Present for about one day · the contributor is a male aged 40–49 · reported lesion symptoms include bothersome appearance · the patient described the issue as a rash · this is a close-up image: 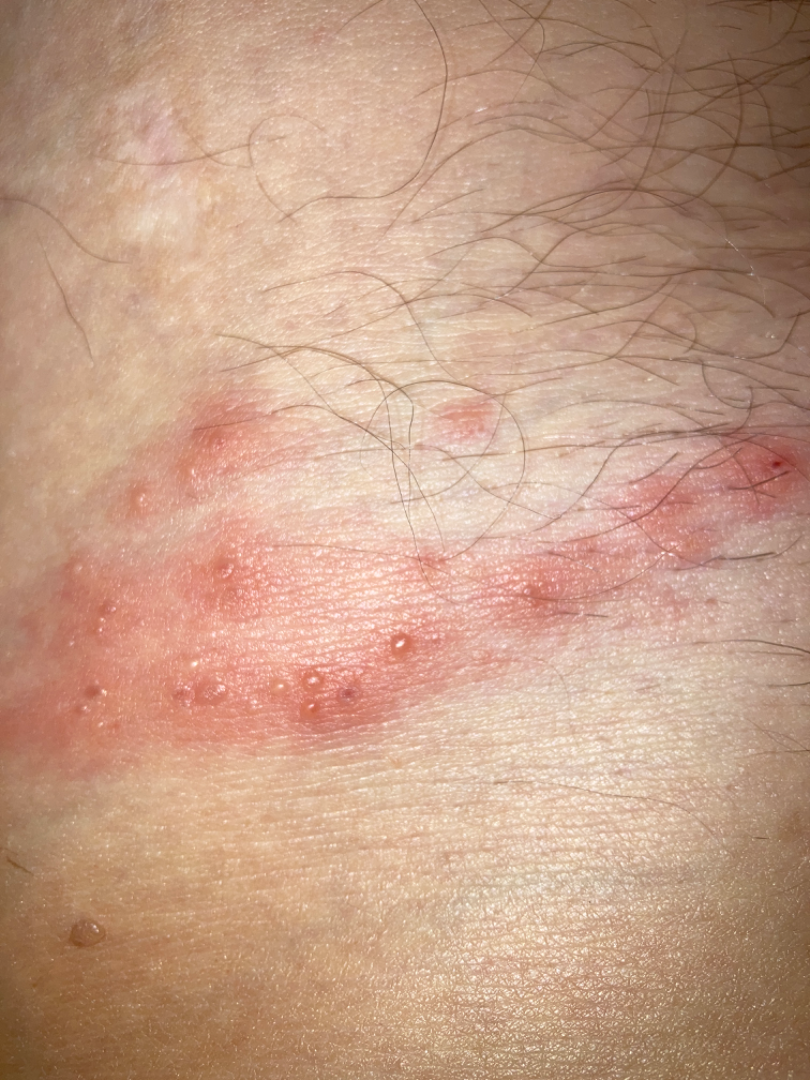A single dermatologist reviewed the case: in keeping with Herpes Zoster.